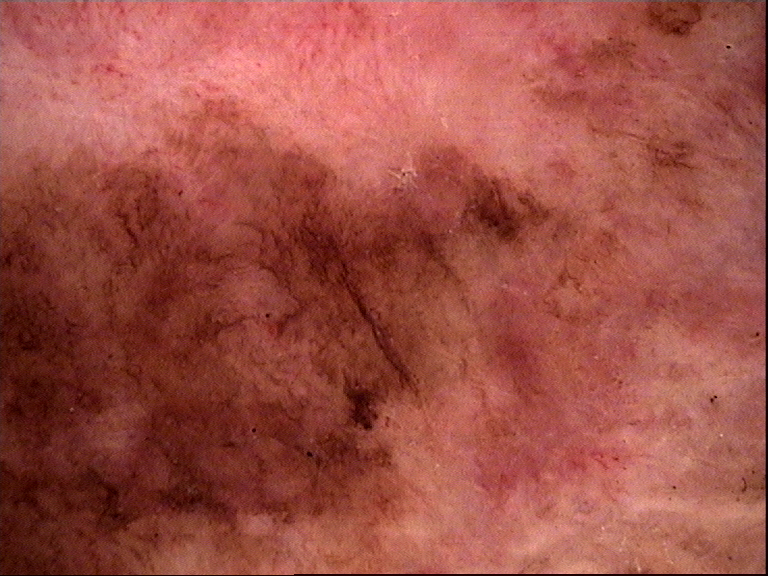* image type — dermatoscopy
* subtype — keratinocytic
* diagnosis — Bowen's disease (biopsy-proven)